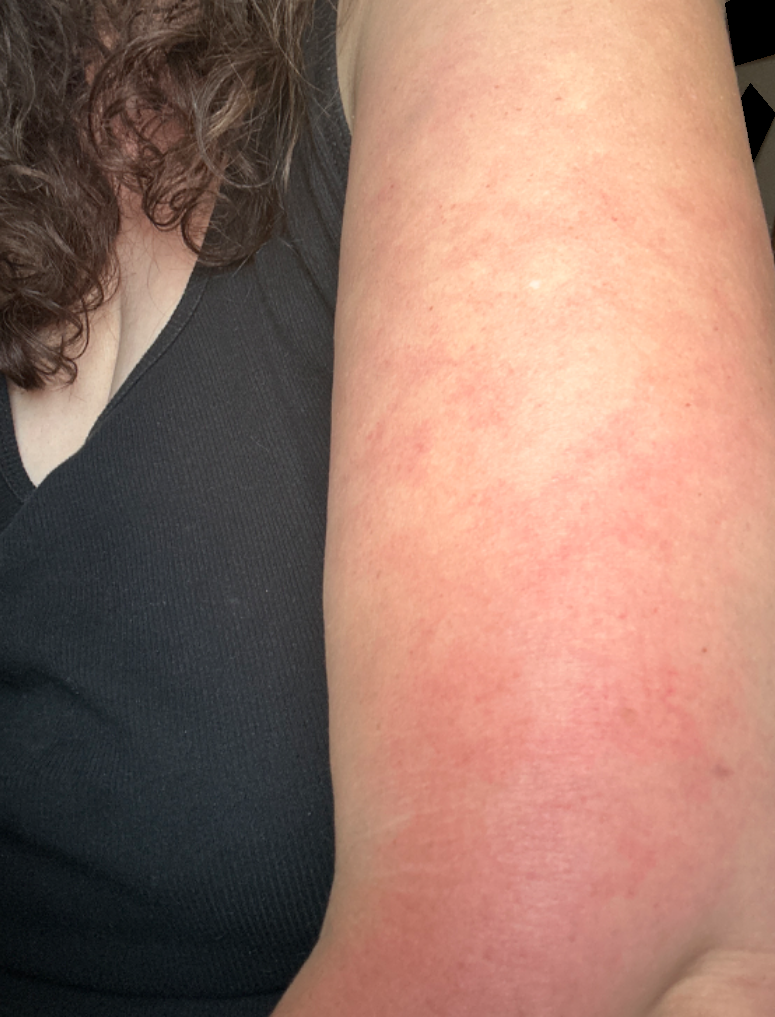location = arm | subject = female, age 40–49 | patient describes the issue as = a rash | duration = about one day | shot type = at an angle | described texture = raised or bumpy | impression = favoring Photodermatitis; an alternative is Keratosis pilaris; a remote consideration is Allergic Contact Dermatitis.